A skin lesion imaged with a dermatoscope:
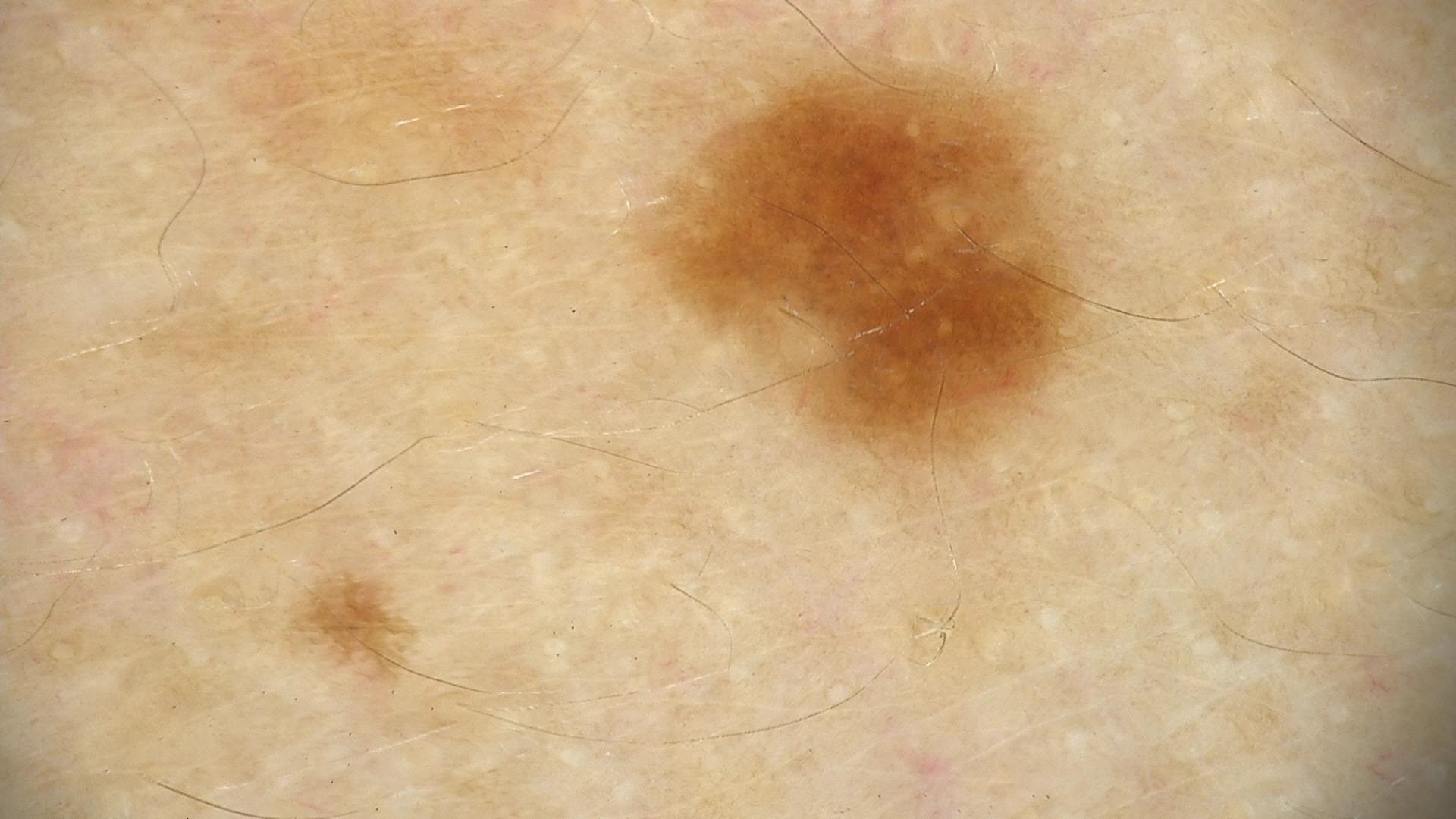Classified as a benign lesion — a dysplastic junctional nevus.